Female contributor, age 30–39. The lesion involves the arm and leg. This image was taken at a distance: 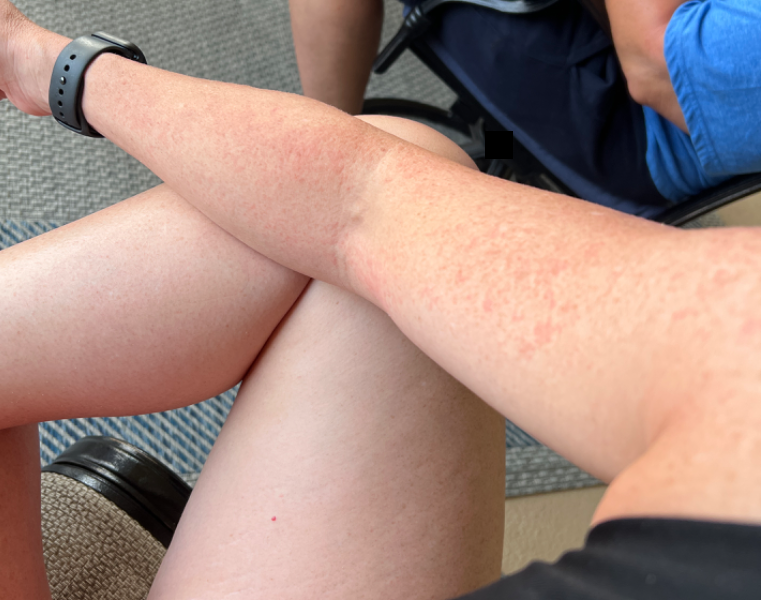{"assessment": "indeterminate"}